A wide-field clinical photograph of a skin lesion. A female patient roughly 80 years of age. The patient was assessed as skin type II.
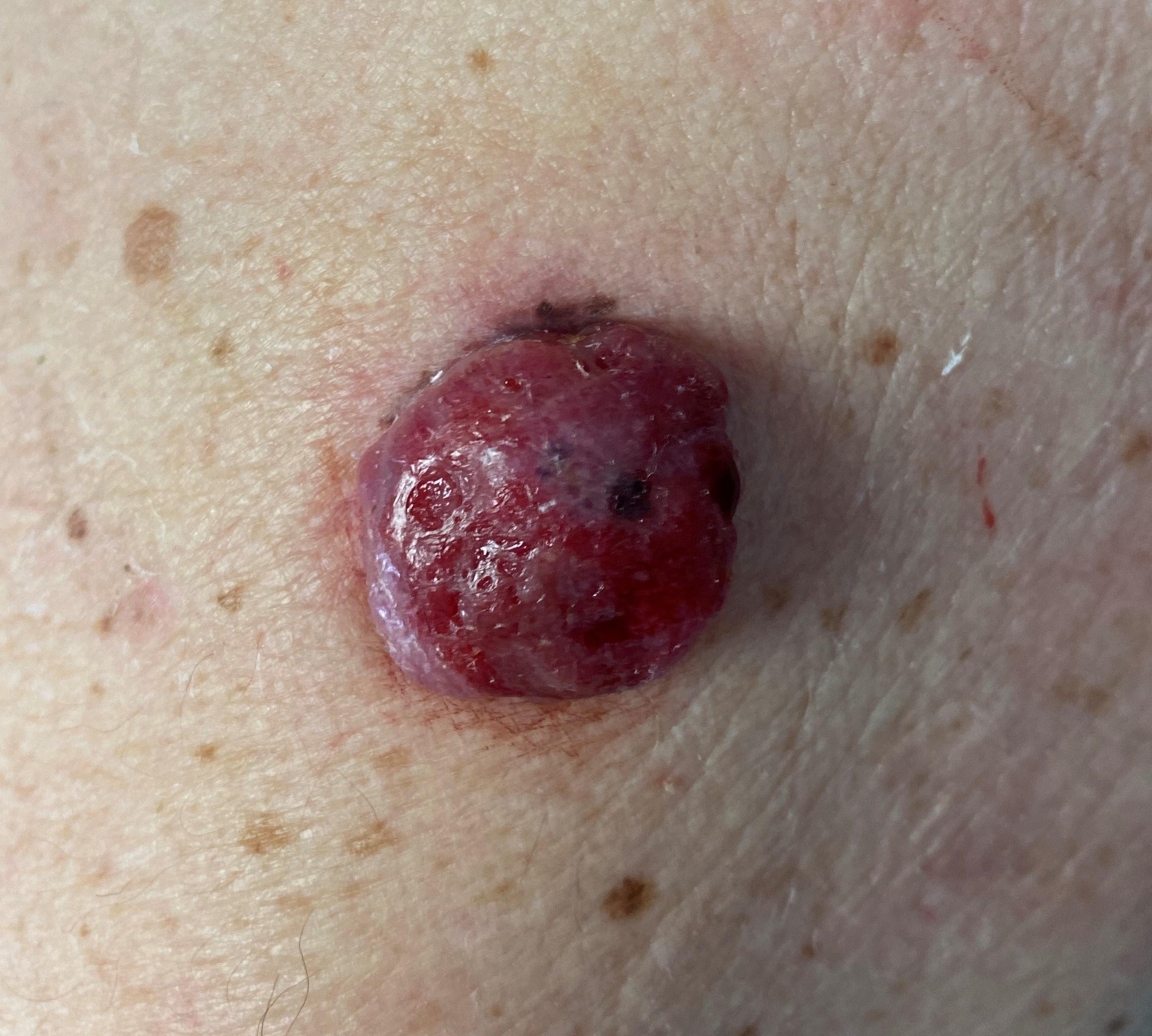The lesion is located on an upper extremity.
On biopsy, the diagnosis was a melanoma.